The photo was captured at a distance; the subject is 50–59, female; the lesion involves the leg.
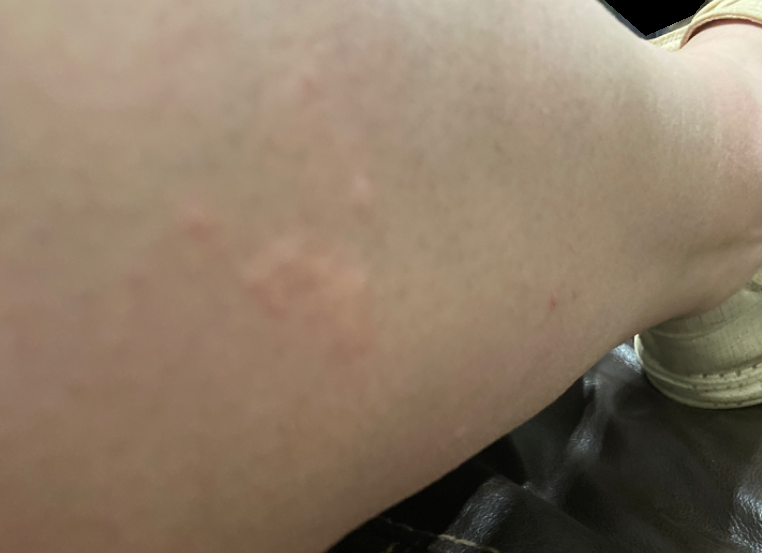The case was difficult to assess from the available photograph.
The contributor reports the condition has been present for about one day.
Symptoms reported: itching.
The patient described the issue as a rash.
Fitzpatrick phototype IV; human graders estimated Monk Skin Tone 2 (US pool) or 4 (India pool).